A female subject, in their mid-30s. This is a dermoscopic photograph of a skin lesion.
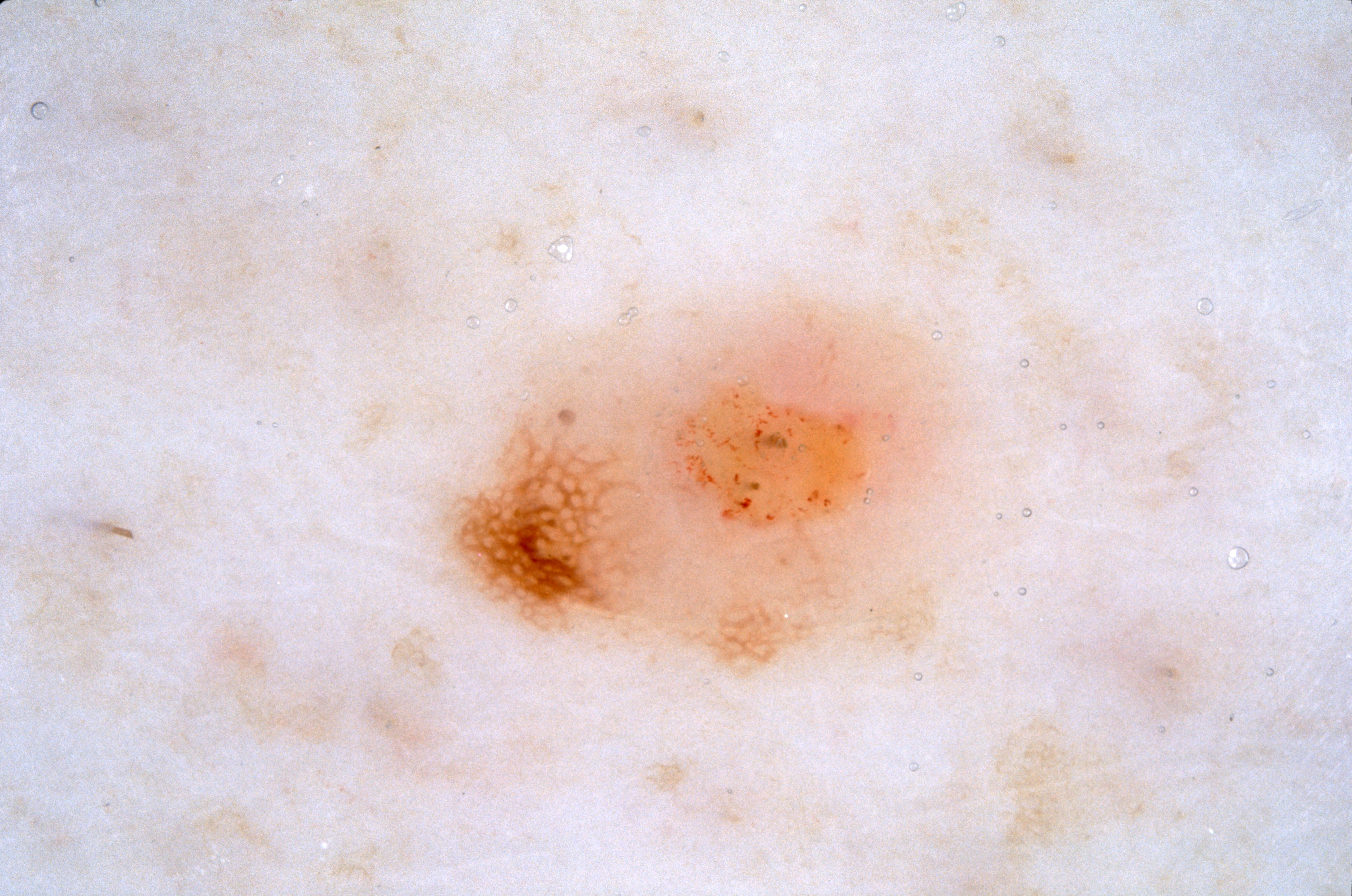Case summary: The dermoscopic pattern shows pigment network. With coordinates (x1, y1, x2, y2), the lesion is bounded by 413 271 994 699. Conclusion: Expert review diagnosed this as a melanocytic nevus, a benign lesion.